A skin lesion imaged with a dermatoscope: 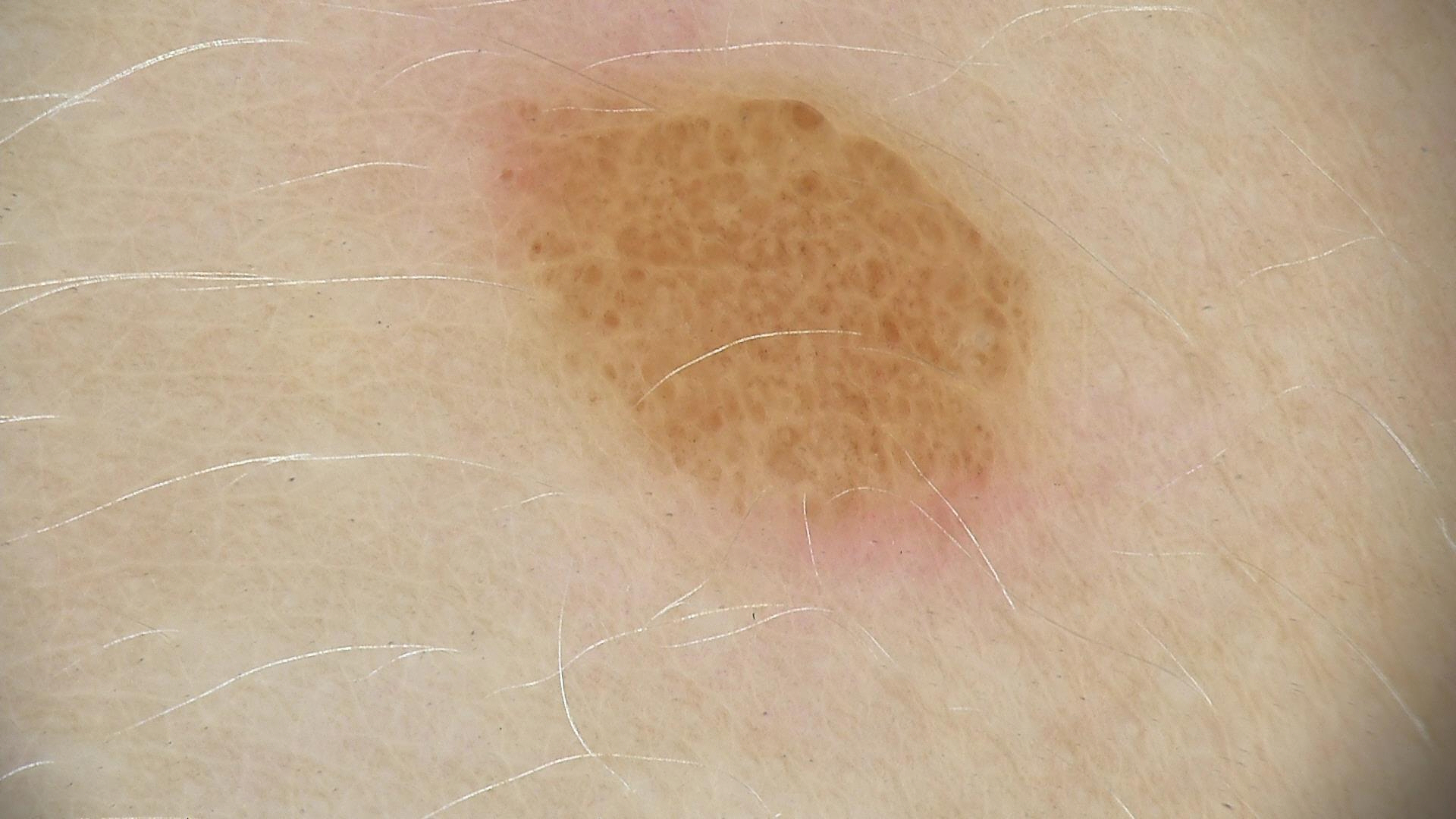Consistent with a dysplastic compound nevus.